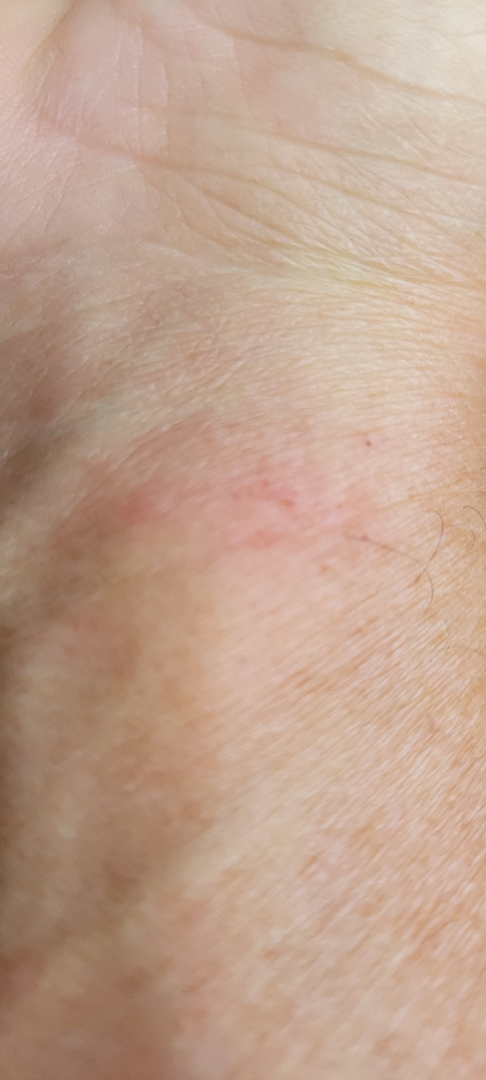The image was not sufficient for the reviewer to characterize the skin condition. Texture is reported as raised or bumpy. The subject is 60–69, male. The contributor notes the condition has been present for less than one week. Located on the arm. Symptoms reported: itching. Close-up view. Self-categorized by the patient as skin that appeared healthy to them.